Present for less than one week · the contributor reports itching, burning and enlargement · female contributor, age 70–79 · an image taken at a distance — 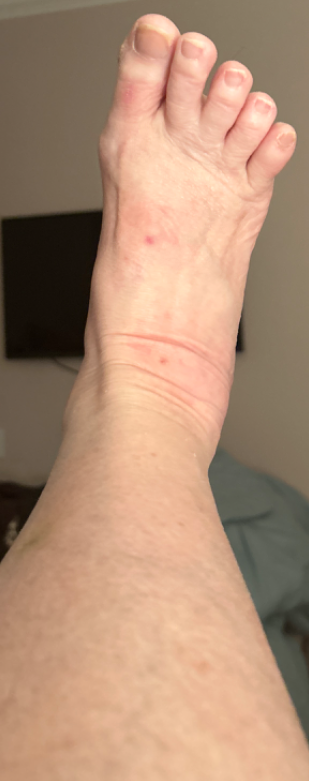| key | value |
|---|---|
| assessment | unable to determine |